A dermoscopy image of a single skin lesion.
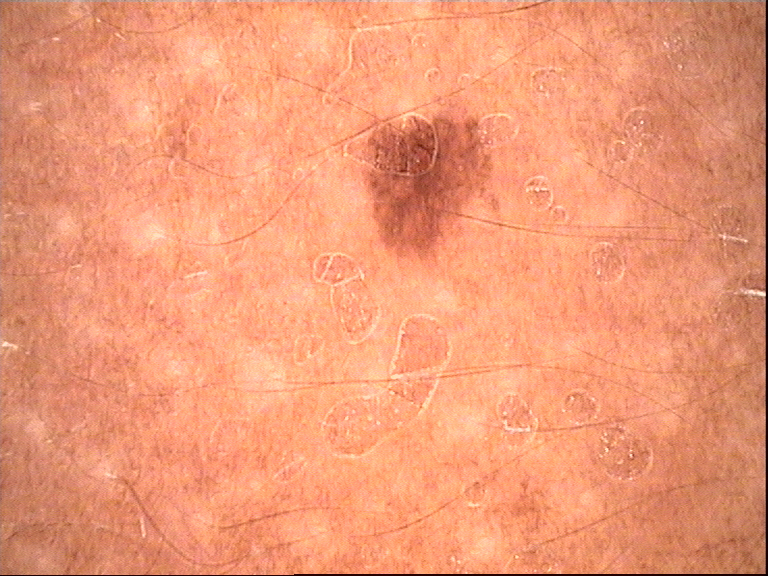The diagnostic label was a dysplastic junctional nevus.